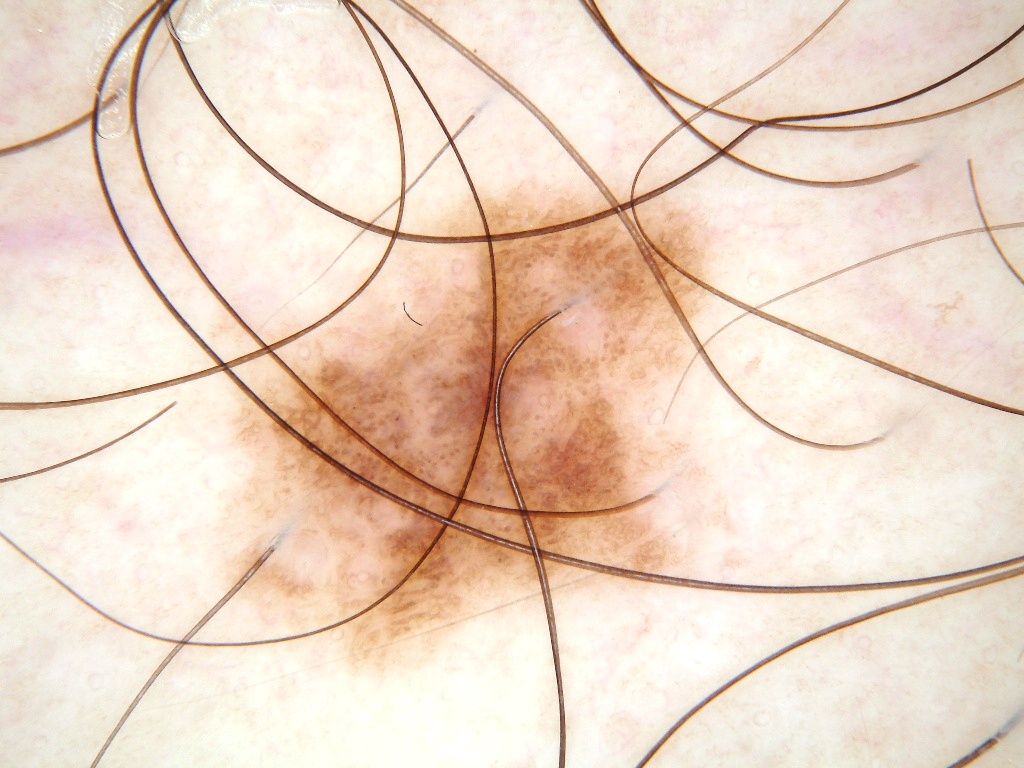A skin lesion imaged with a dermatoscope.
A male patient aged 28 to 32.
On dermoscopy, the lesion shows pigment network and globules.
The lesion covers approximately 27% of the dermoscopic field.
The lesion occupies the region left=196, top=161, right=755, bottom=691.
Clinically diagnosed as a melanocytic nevus.